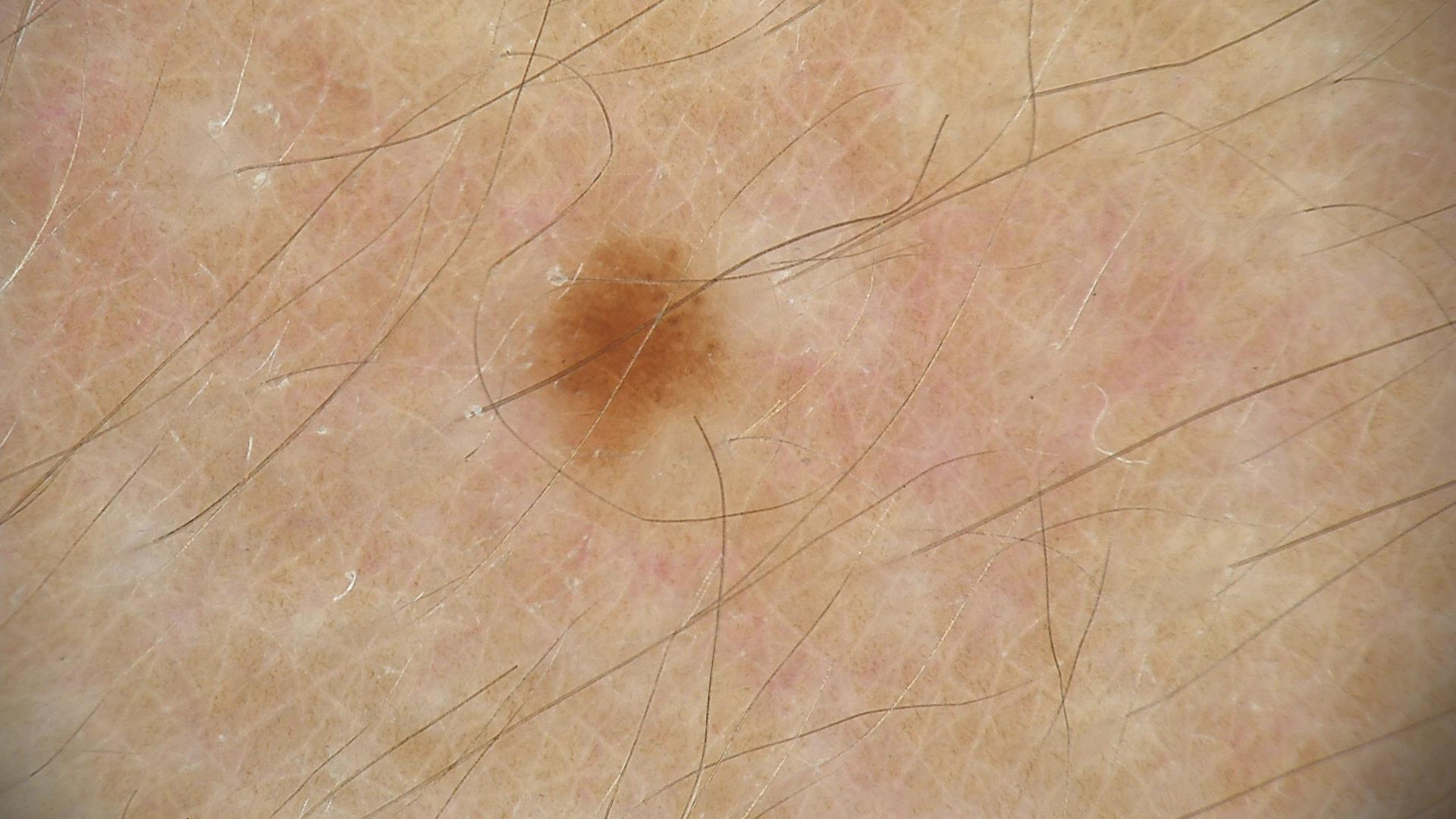A skin lesion imaged with a dermatoscope. Diagnosed as a benign lesion — a dysplastic junctional nevus.